This is a dermoscopic photograph of a skin lesion:
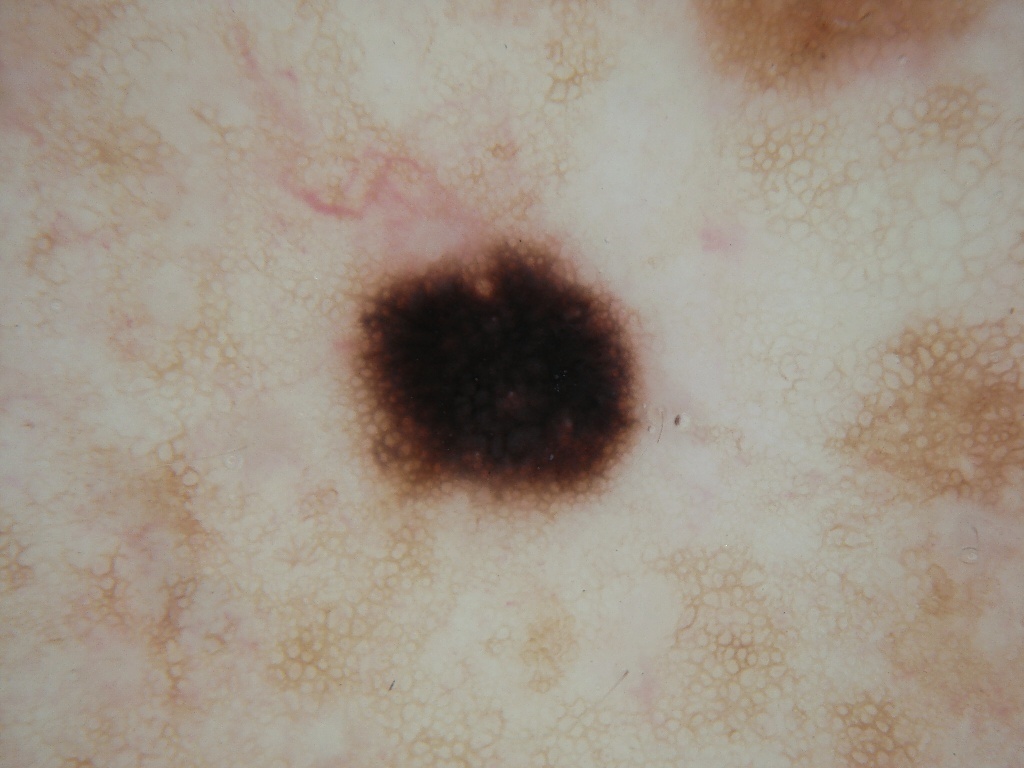The lesion's extent is [346, 235, 647, 510]. Dermoscopic examination shows no globules or streaks. Diagnosed as a benign skin lesion.